Located on the arm; the photograph is a close-up of the affected area.
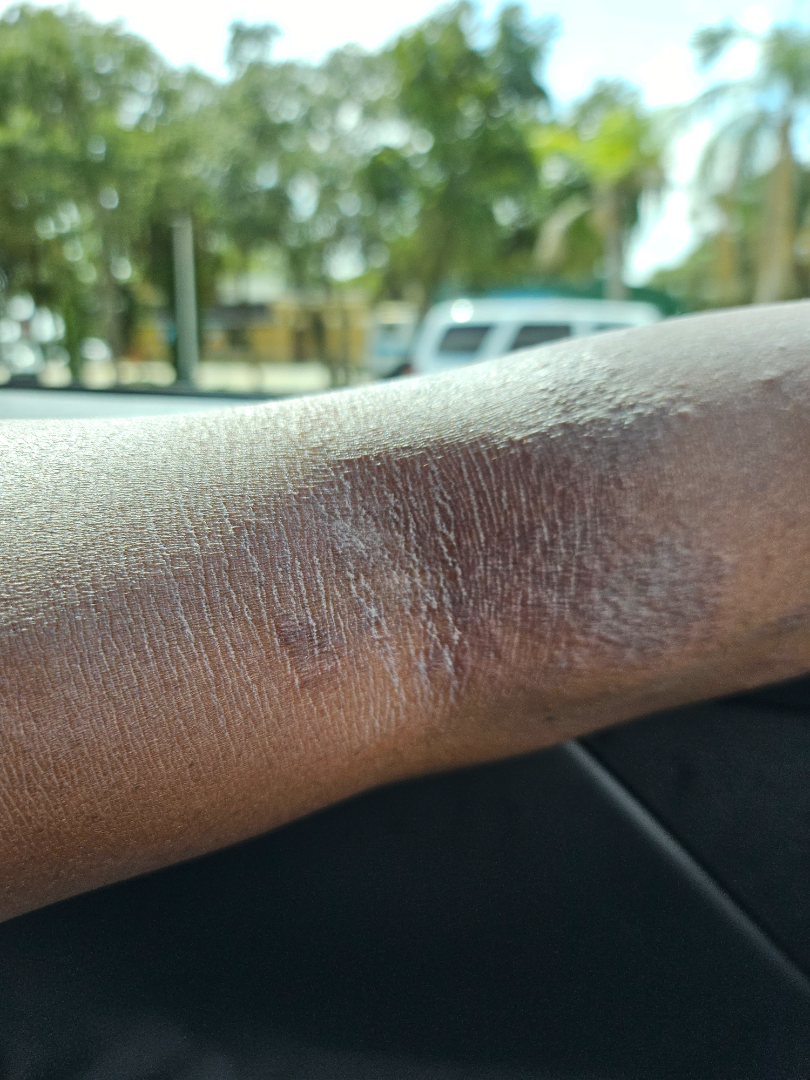FST V; non-clinician graders estimated 7 on the Monk skin tone scale.
Self-categorized by the patient as a rash.
No constitutional symptoms were reported.
Texture is reported as raised or bumpy.
The condition has been present for less than one week.
Symptoms reported: itching.
In keeping with Eczema.